A clinical overview photograph of a skin lesion; a female patient aged 68 to 72; the patient is Fitzpatrick phototype II — 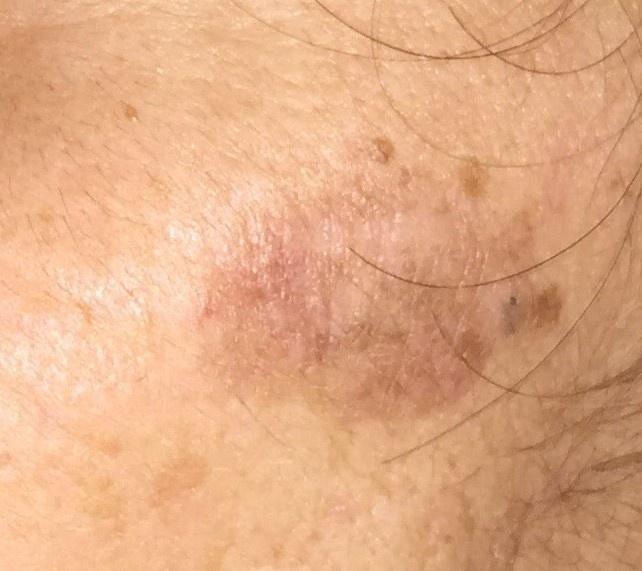Findings:
• body site: the head or neck
• diagnostic label: Squamous cell carcinoma (biopsy-proven)